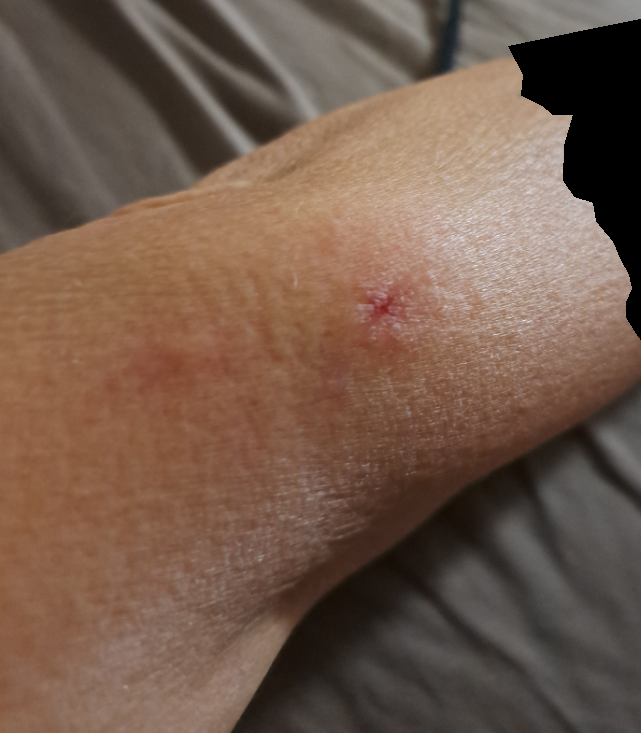assessment = ungradable on photographic review
body site = leg and arm
duration = less than one week
symptoms = itching
patient describes the issue as = a rash
skin tone = Fitzpatrick phototype IV; human graders estimated 3 on the MST
texture = raised or bumpy and fluid-filled
image framing = at a distance